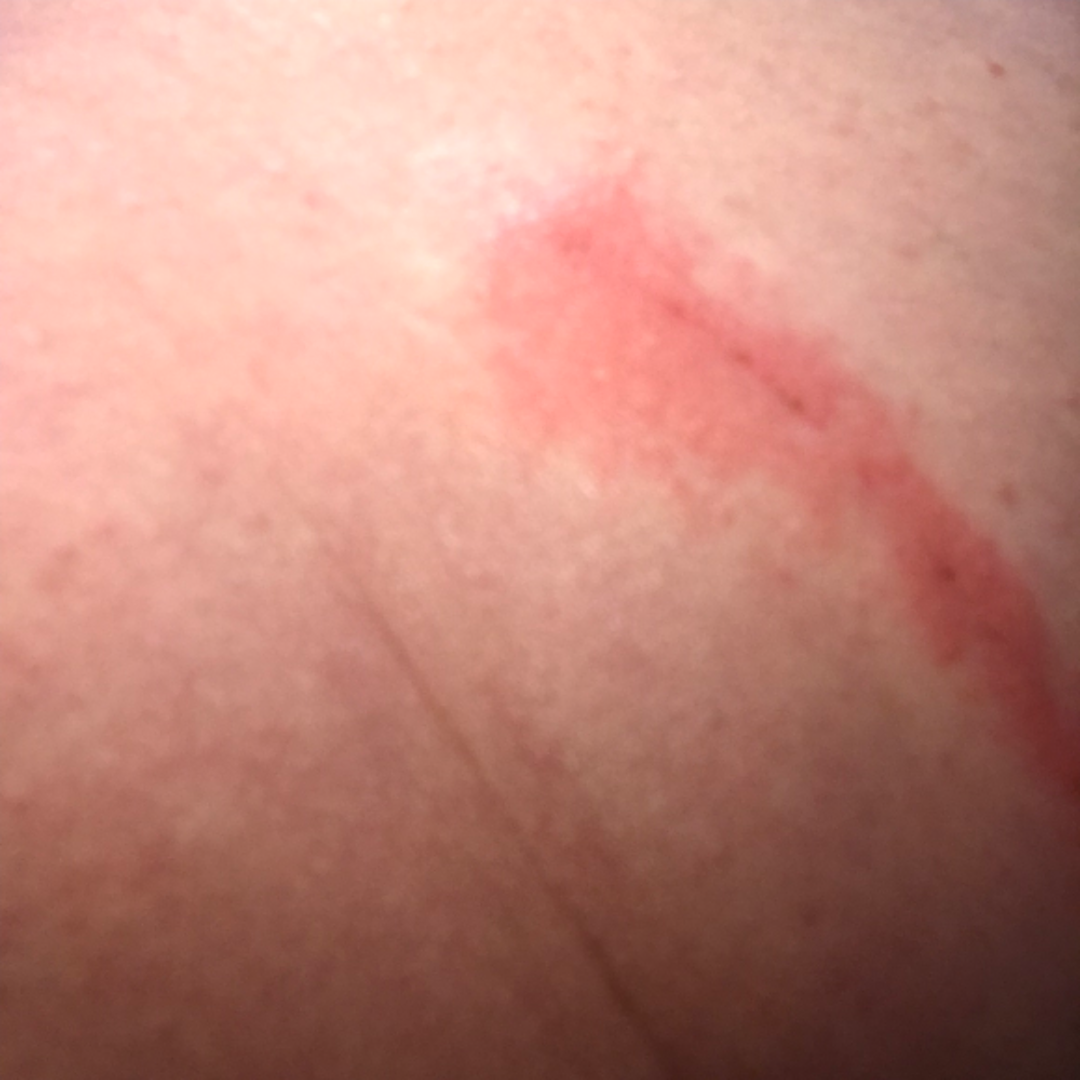<dermatology_case>
  <assessment>ungradable on photographic review</assessment>
  <duration>less than one week</duration>
  <texture>raised or bumpy</texture>
  <body_site>back of the torso</body_site>
  <patient_category>a rash</patient_category>
  <shot_type>close-up</shot_type>
</dermatology_case>